FST IV; non-clinician graders estimated Monk Skin Tone 5 (US pool) or 4 (India pool). The patient notes itching and pain. The patient described the issue as a rash. A close-up photograph. The lesion involves the arm.
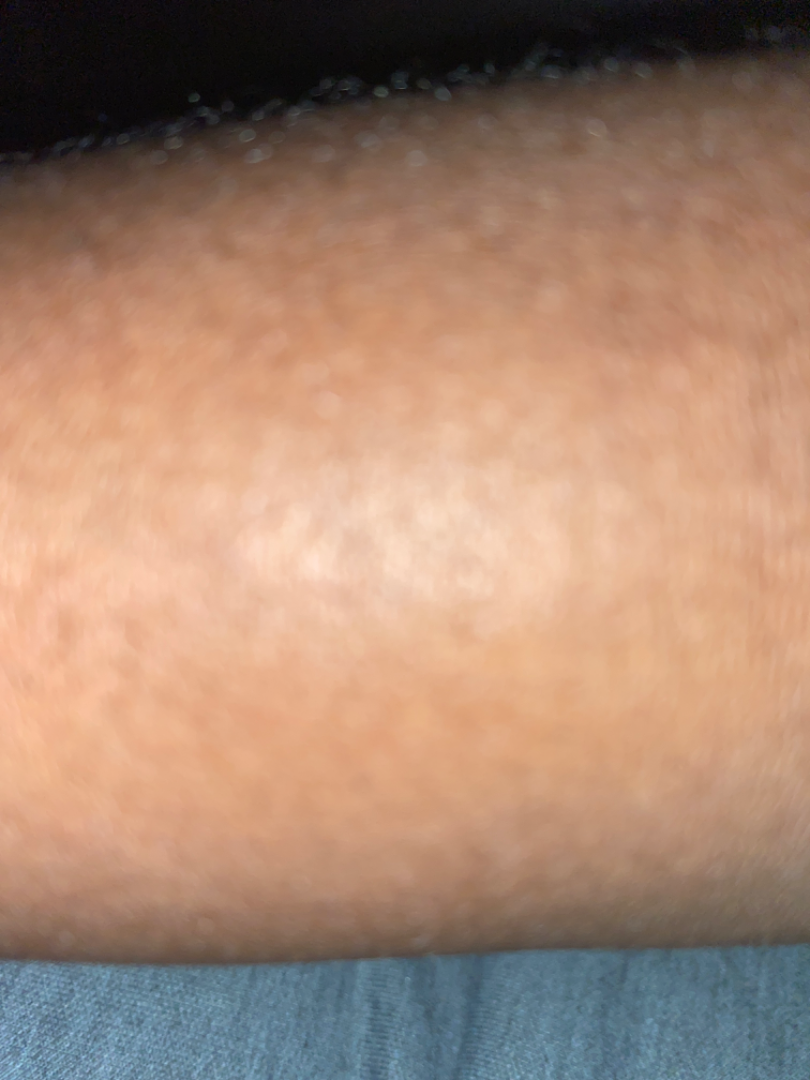Case summary:
- assessment · not assessable